No relevant systemic symptoms · the patient is a female aged 30–39 · close-up view · the condition has been present for one to three months · Fitzpatrick skin type V · texture is reported as raised or bumpy: 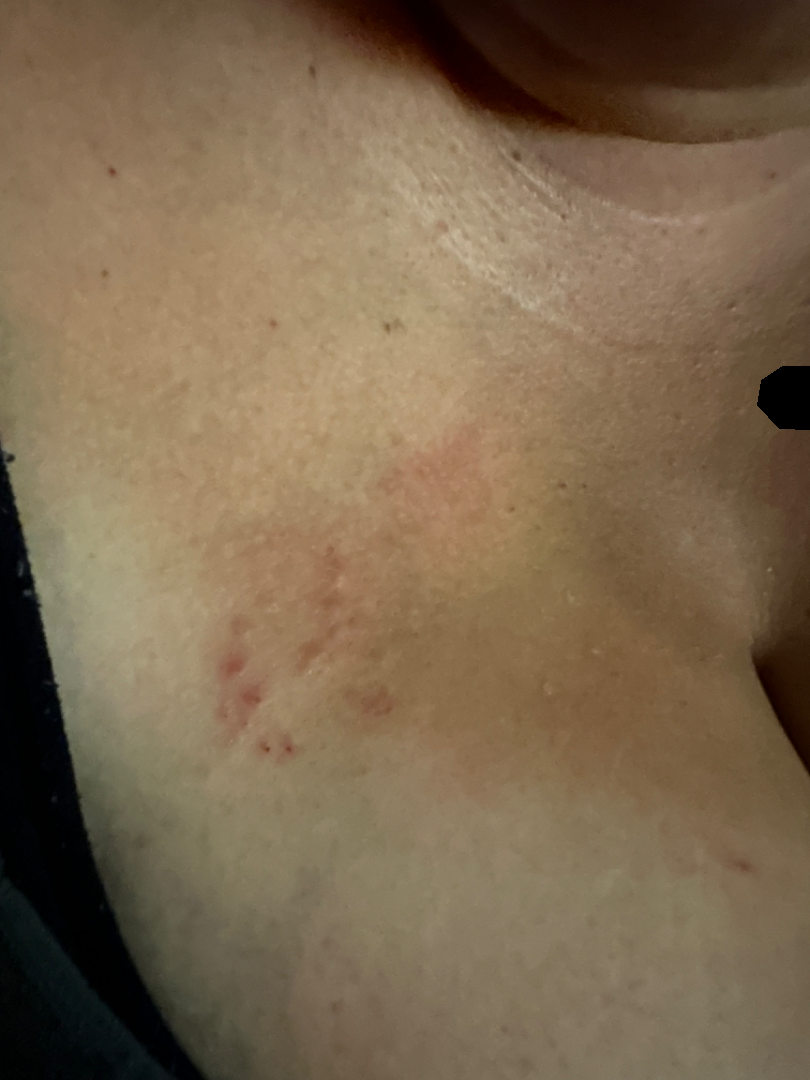differential = single-reviewer assessment: Scar Condition and Skin atrophy were each considered, in no particular order.